The patient is a female aged 18–29. Located on the head or neck. This image was taken at an angle — 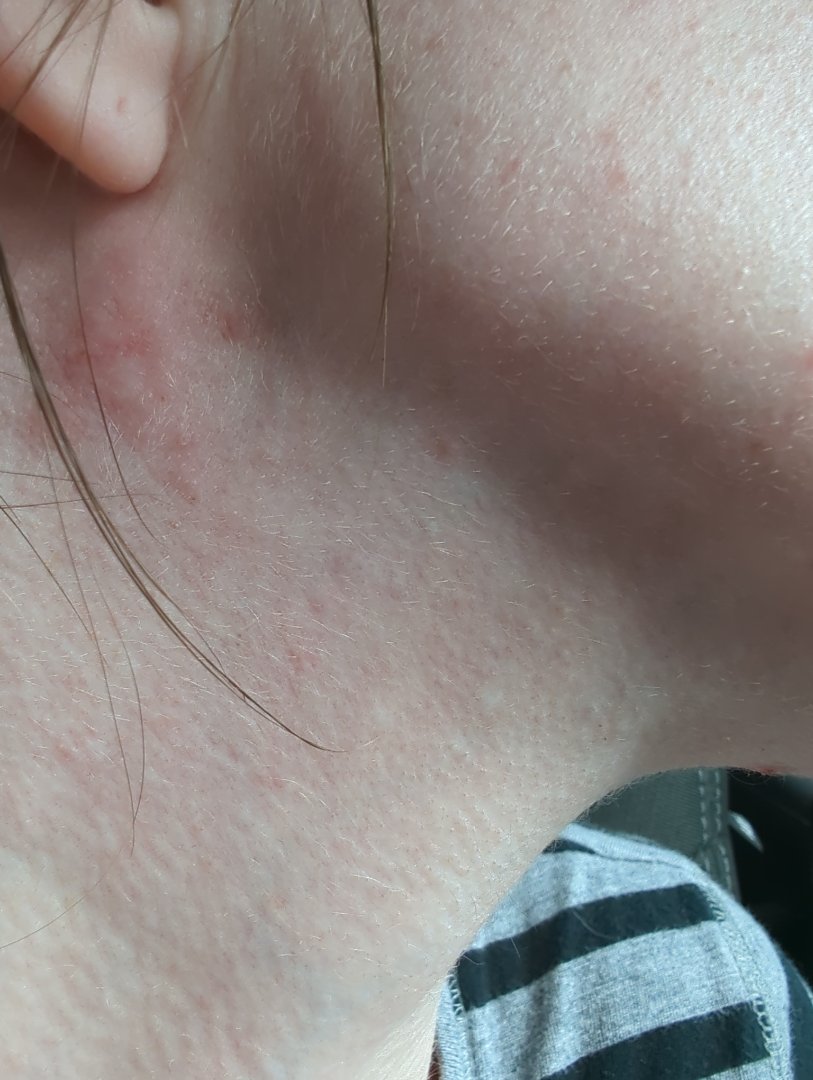Reviewed remotely by three dermatologists: the leading impression is Acne; an alternative is Seborrheic Dermatitis; with consideration of Allergic Contact Dermatitis.